An image taken at a distance.
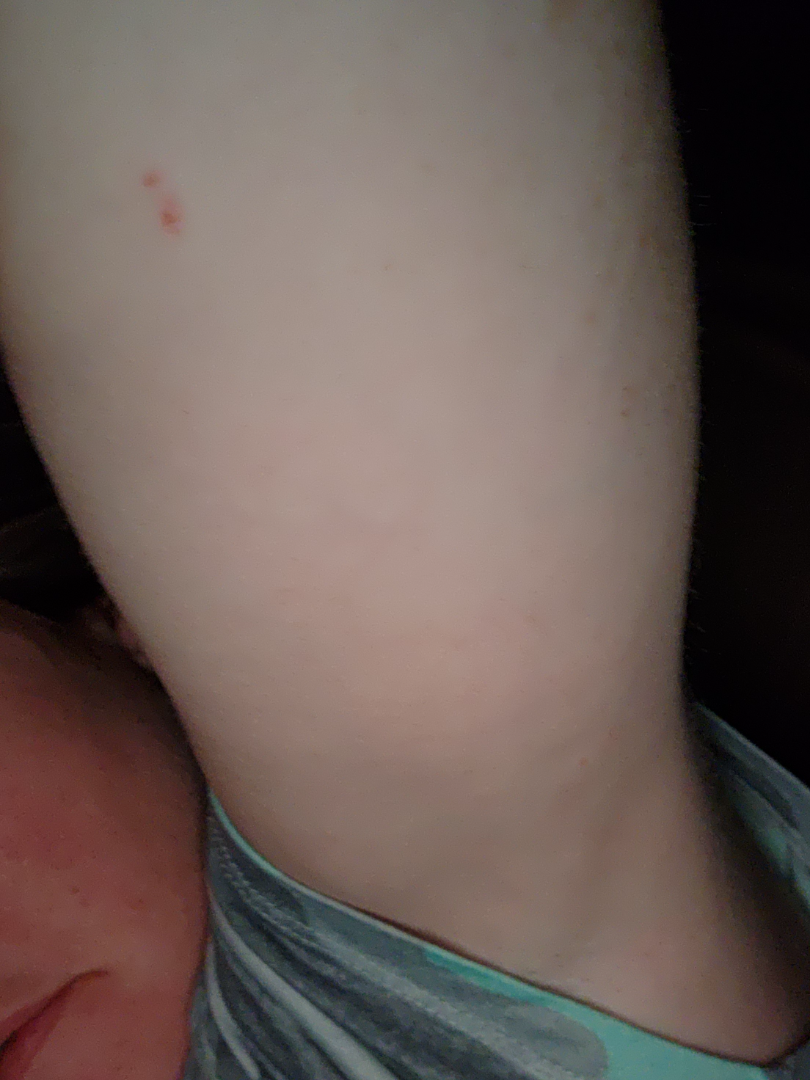Skin tone: human graders estimated MST 2. The reviewing clinician's impression was: Allergic Contact Dermatitis (considered); Irritant Contact Dermatitis (considered).